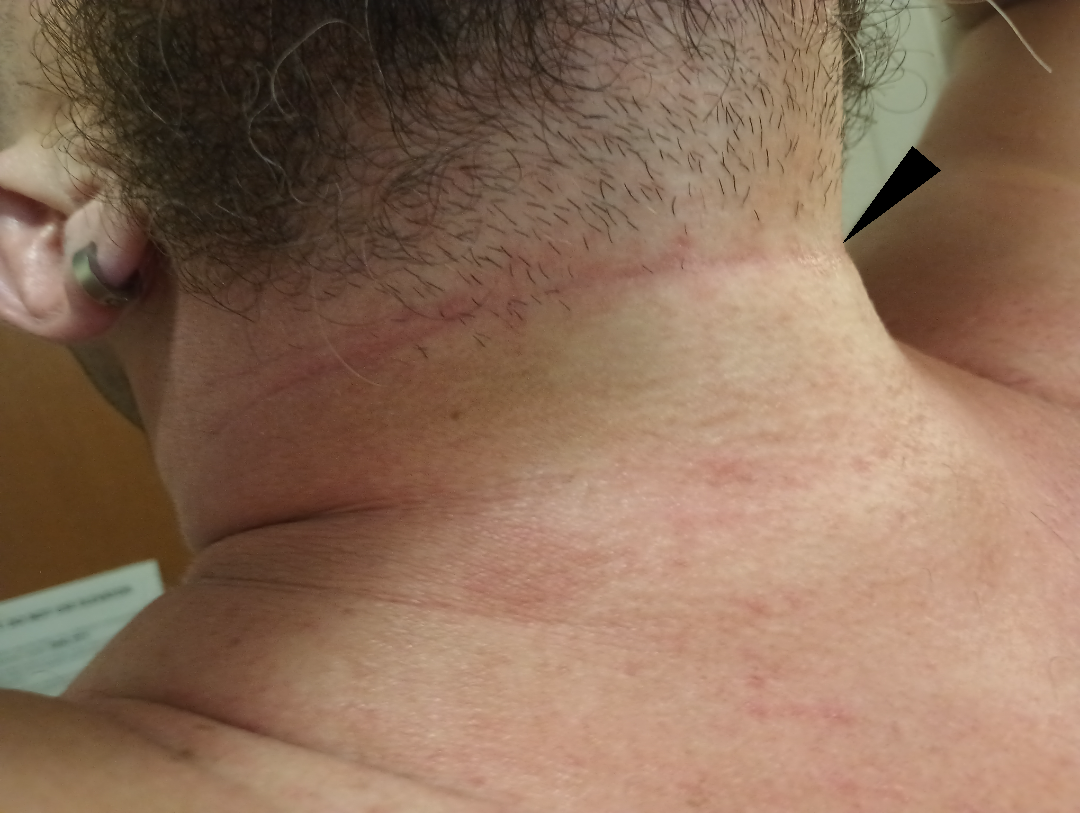The case was difficult to assess from the available photograph.